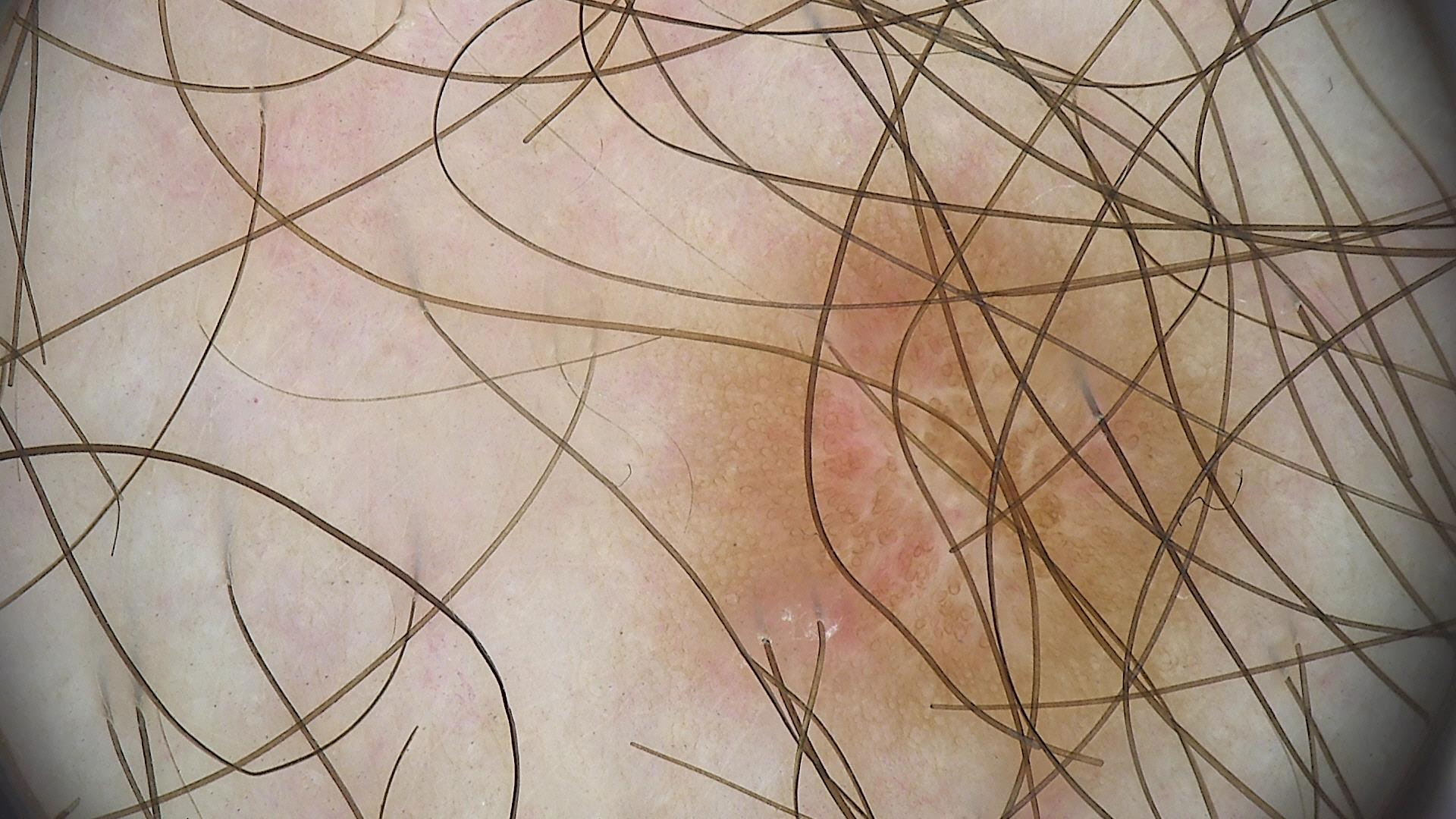Case:
• category: fibro-histiocytic
• diagnosis: dermatofibroma (expert consensus)